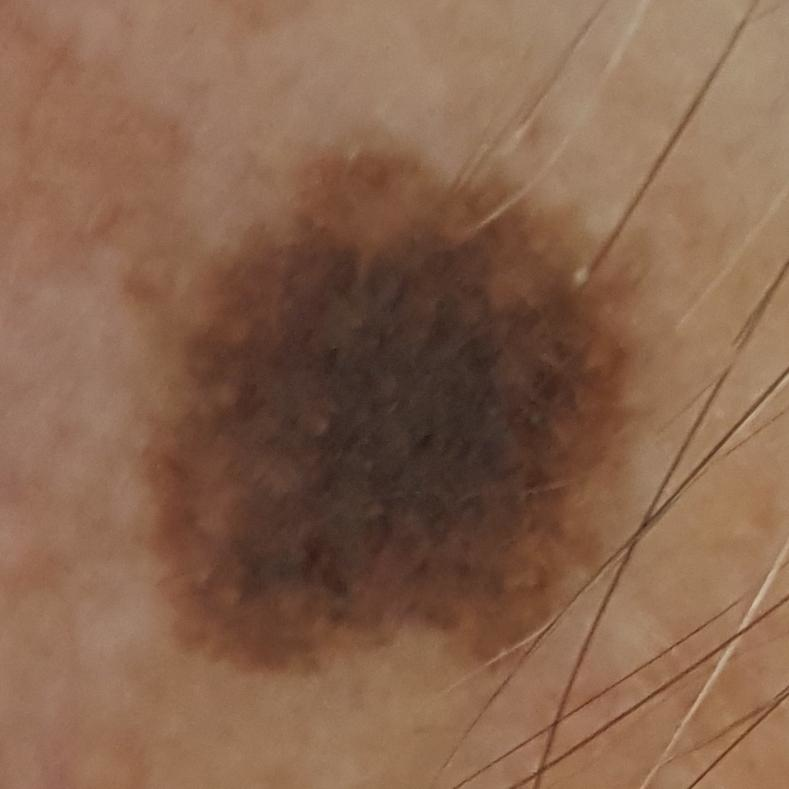Findings:
A smartphone photograph of a skin lesion. A male subject in their early 80s. The lesion was found on an ear. The patient describes that the lesion has changed and has grown, but has not bled and is not elevated.
Conclusion:
Histopathological examination showed a melanoma.